Male subject, age 18–29; this is a close-up image; the affected area is the head or neck — 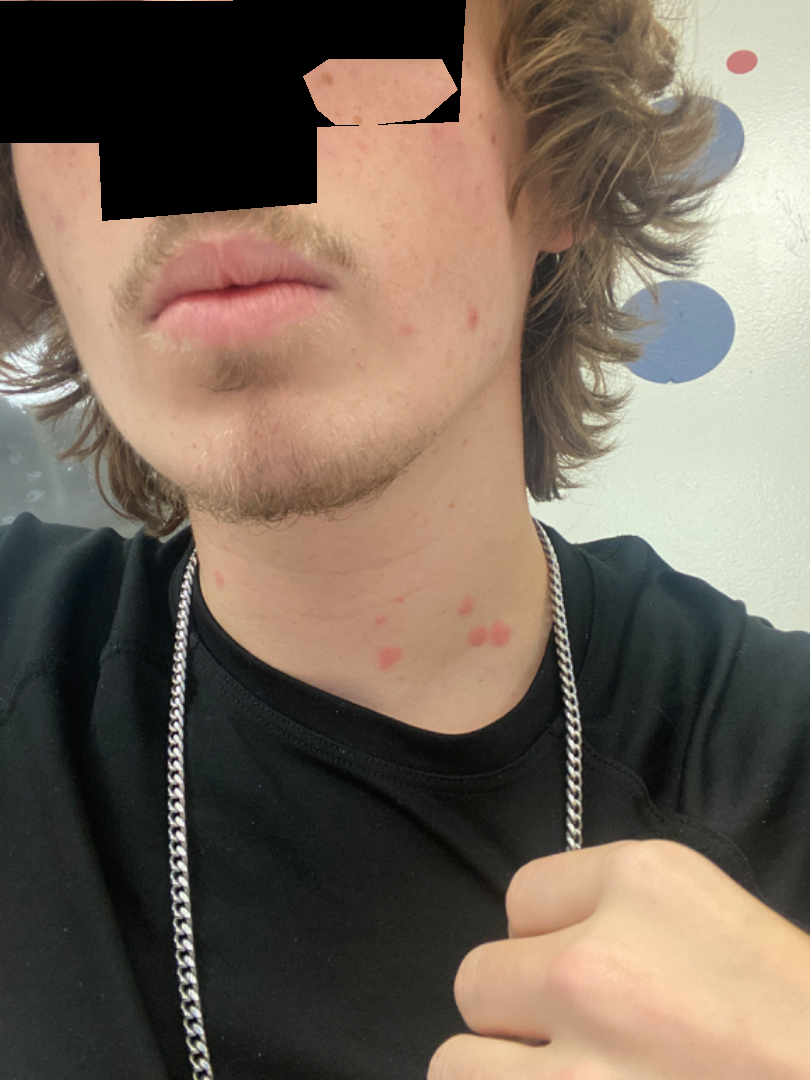Findings: The image was not sufficient for the reviewer to characterize the skin condition.